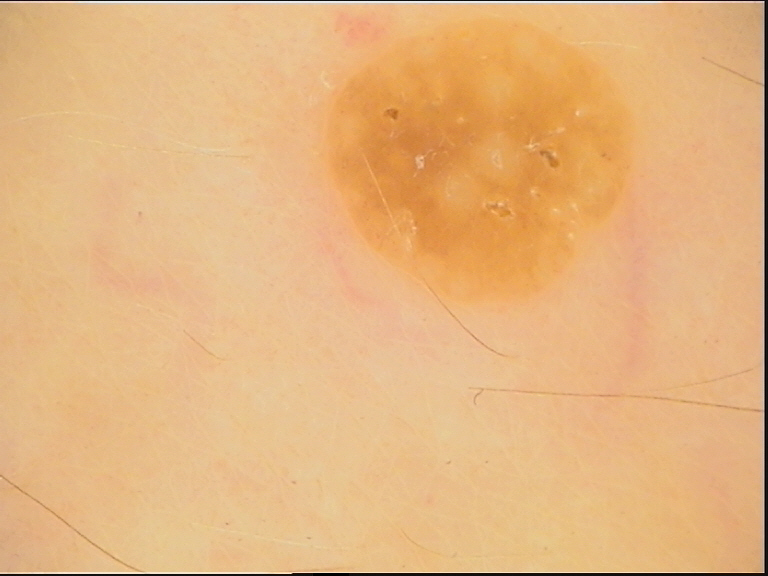Q: What is the imaging modality?
A: dermatoscopy
Q: What is the diagnosis?
A: seborrheic keratosis (expert consensus)